This is a close-up image, the leg is involved.
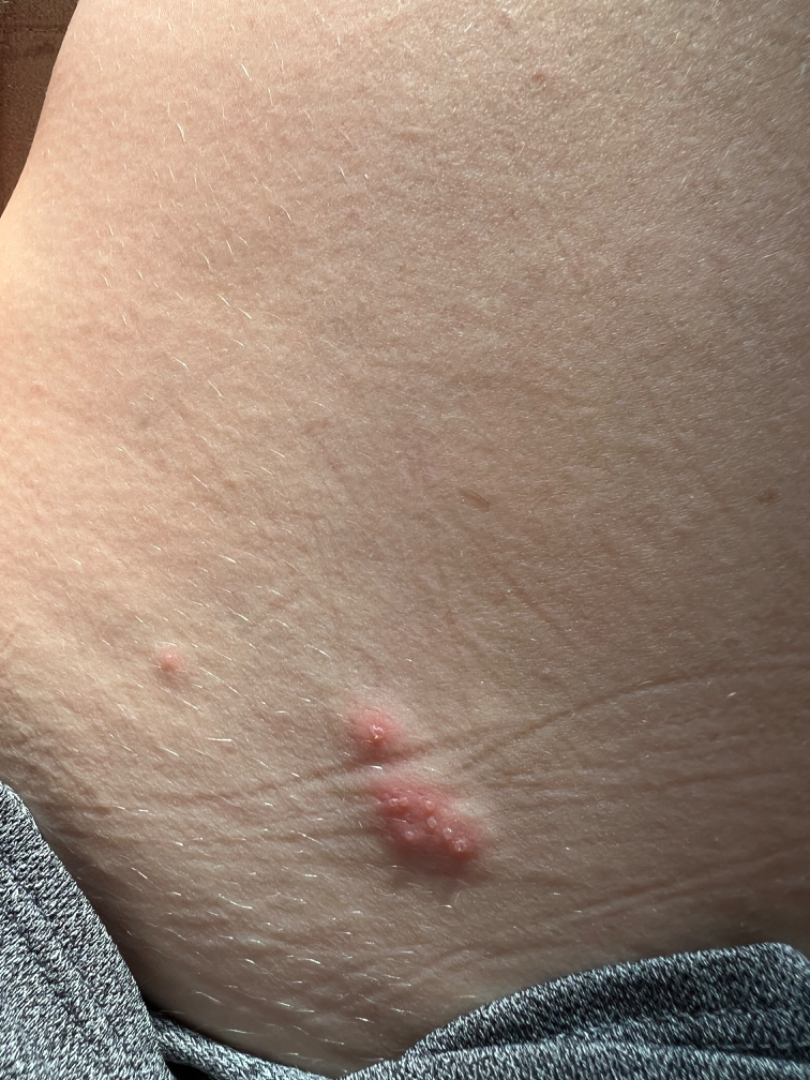Clinical context:
Fitzpatrick phototype III. Texture is reported as fluid-filled and raised or bumpy. Reported lesion symptoms include burning. The patient notes the condition has been present for less than one week.
Assessment:
On photographic review by a dermatologist, the impression is Herpes Simplex.